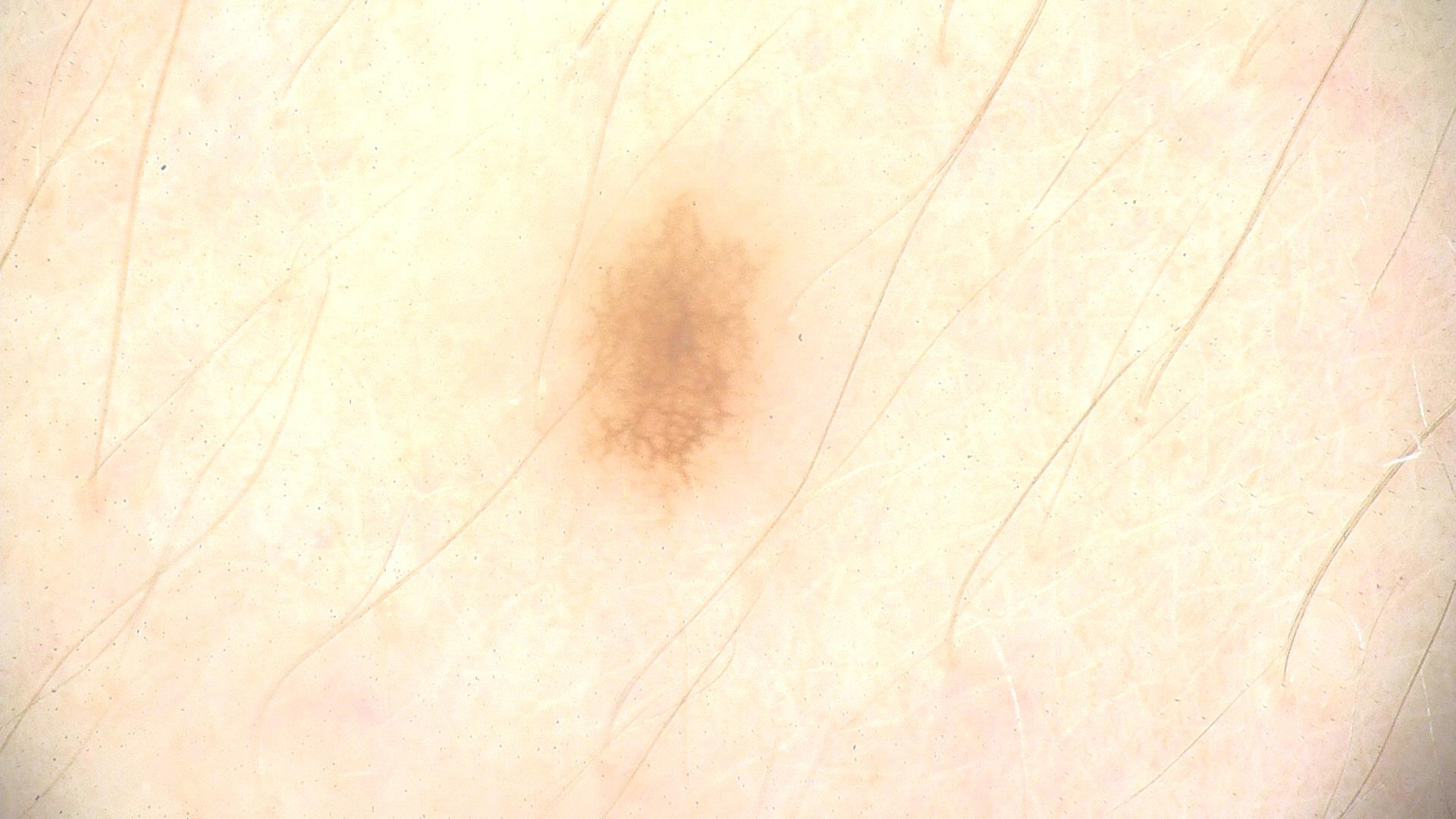assessment = dysplastic junctional nevus (expert consensus)